Dermoscopy of a skin lesion: 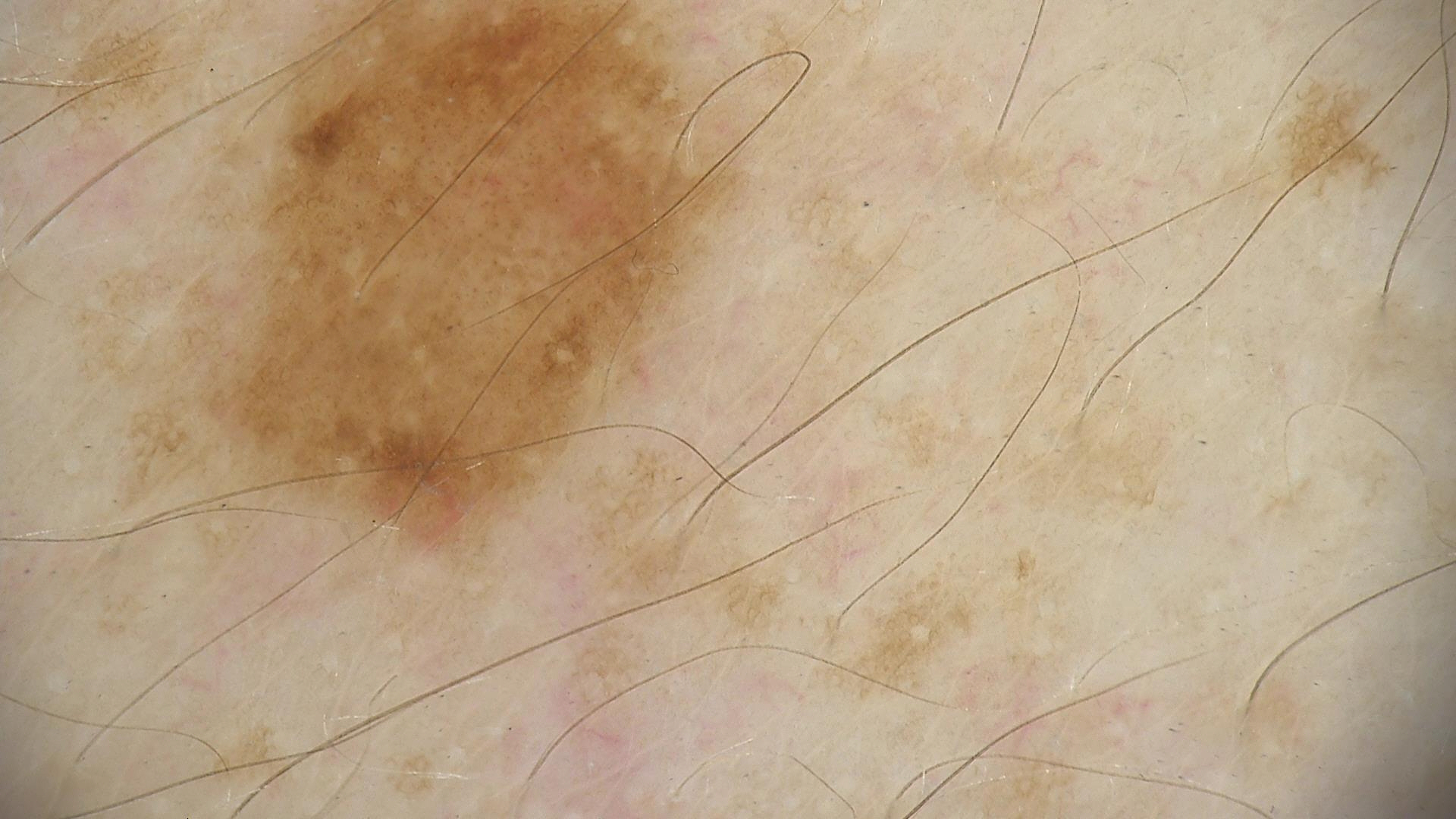Impression: The diagnostic label was a benign lesion — a dysplastic junctional nevus.